A clinical photo of a skin lesion taken with a smartphone · a subject age 55:
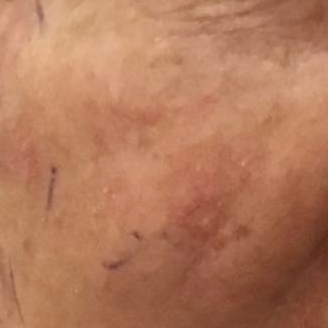Patient and lesion:
Located on the face. Per patient report, the lesion has not bled and has not grown.
Conclusion:
The diagnostic impression was a lesion of indeterminate malignant potential — an actinic keratosis.